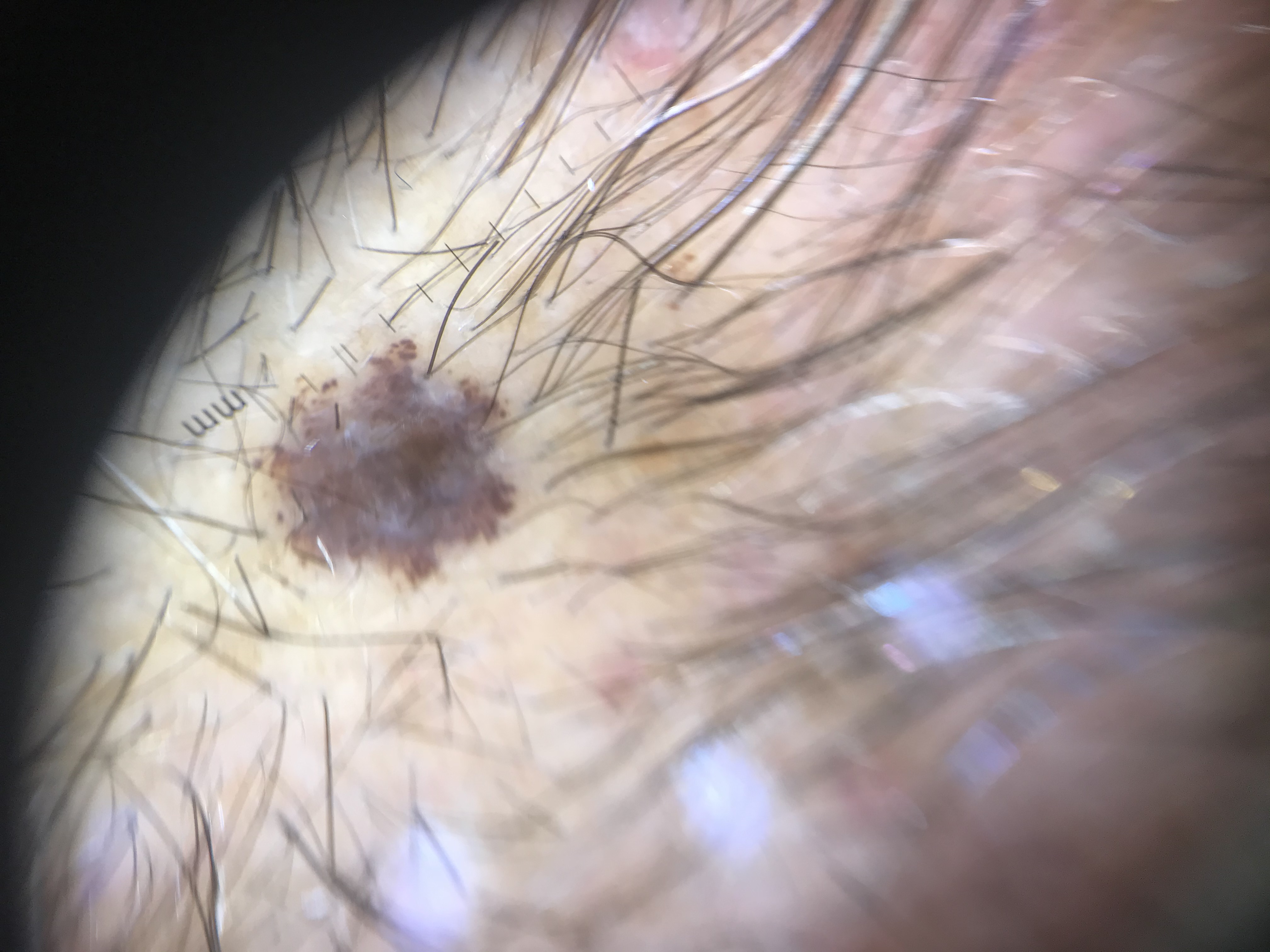The diagnosis was a dysplastic compound nevus.